A moderate number of moles by the patient's own estimate; a clinical photograph of a skin lesion; a male patient 77 years of age; the patient reports a personal history of skin cancer and a personal history of cancer; collected as part of a research study, without a referral diagnosis.
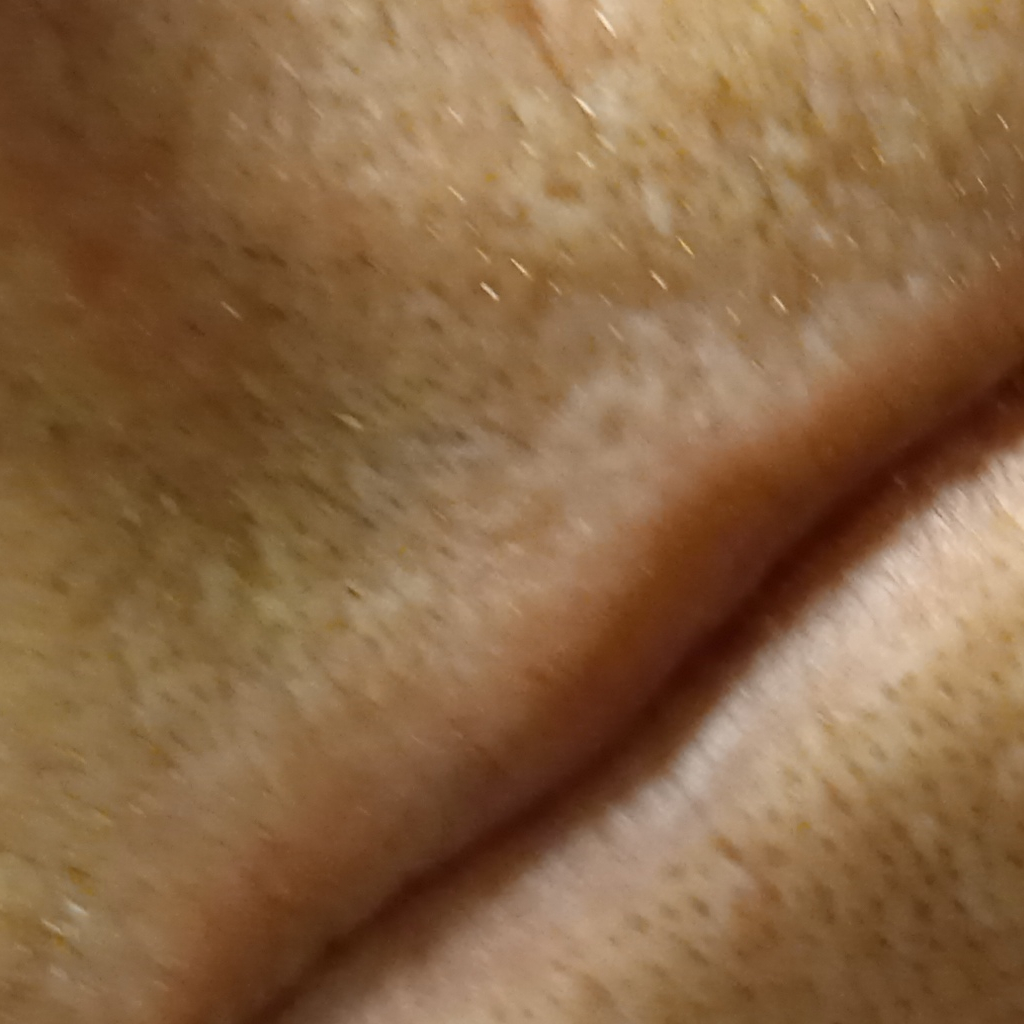Findings:
The lesion measures approximately 6.4 mm.
Conclusion:
The dermatologists' assessment was an actinic keratosis.